A male patient aged approximately 80. A dermoscopy image of a single skin lesion — 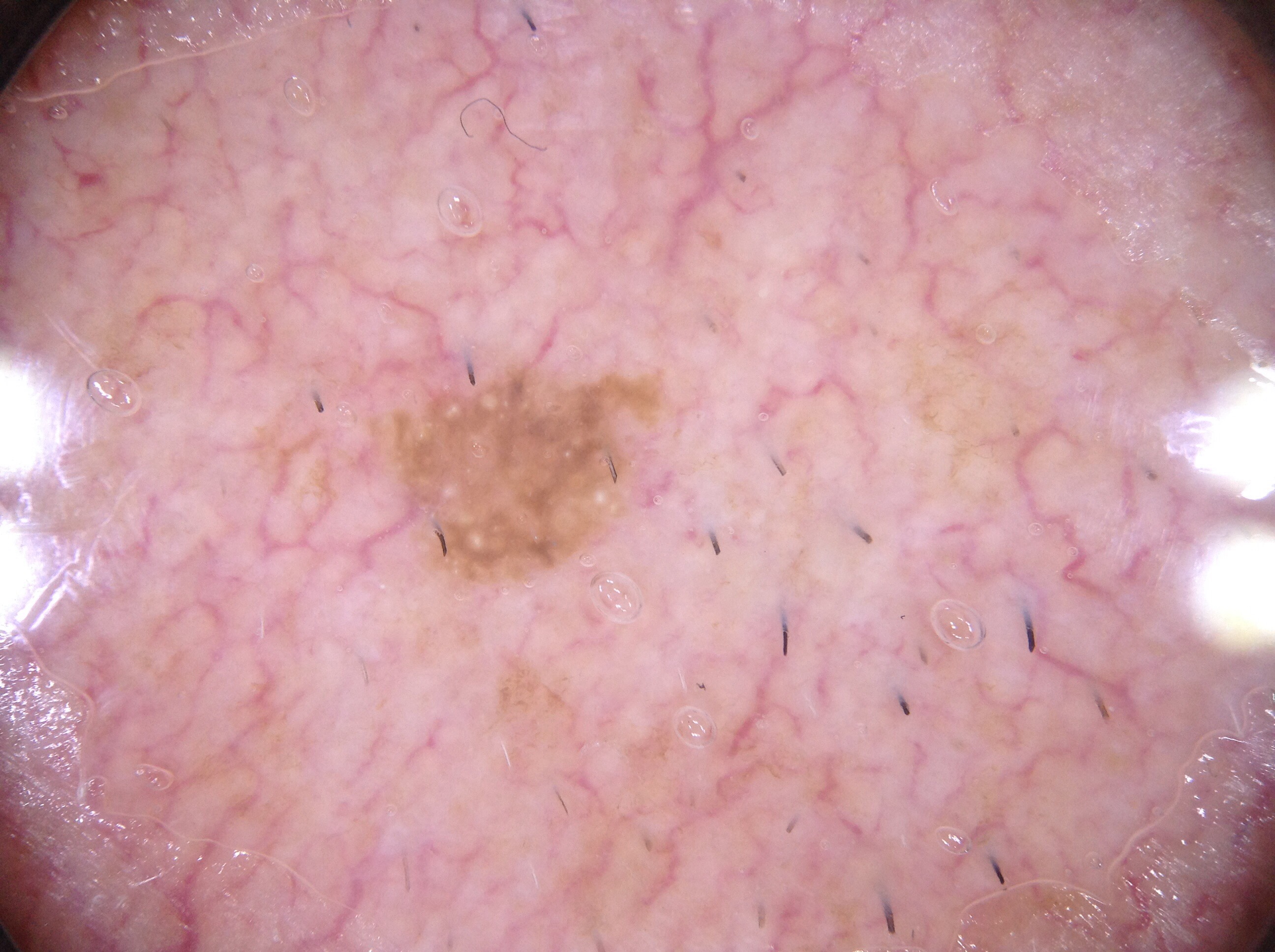Dermoscopic review identifies milia-like cysts. In (x1, y1, x2, y2) order, the lesion is located at 366, 360, 666, 589. The lesion is small relative to the field of view. Diagnosed as a seborrheic keratosis.